The patient reports a personal history of skin cancer; the patient describes having few moles overall; a clinical photograph of a skin lesion; a male patient age 67; the patient says their skin tans without first burning:
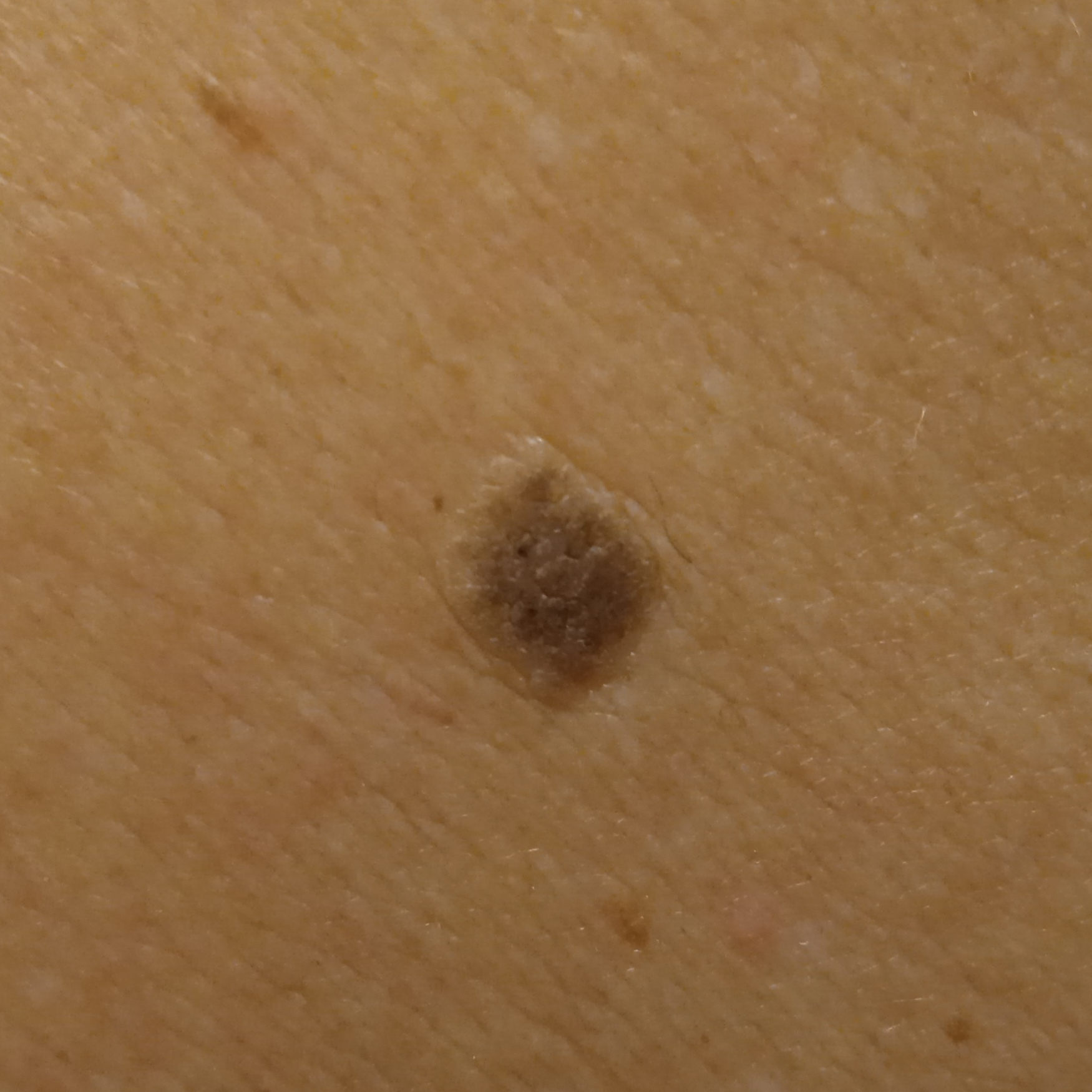The lesion is located on the back. The lesion measures approximately 8.9 mm. The consensus diagnosis for this lesion was a seborrheic keratosis.